This is a close-up image — 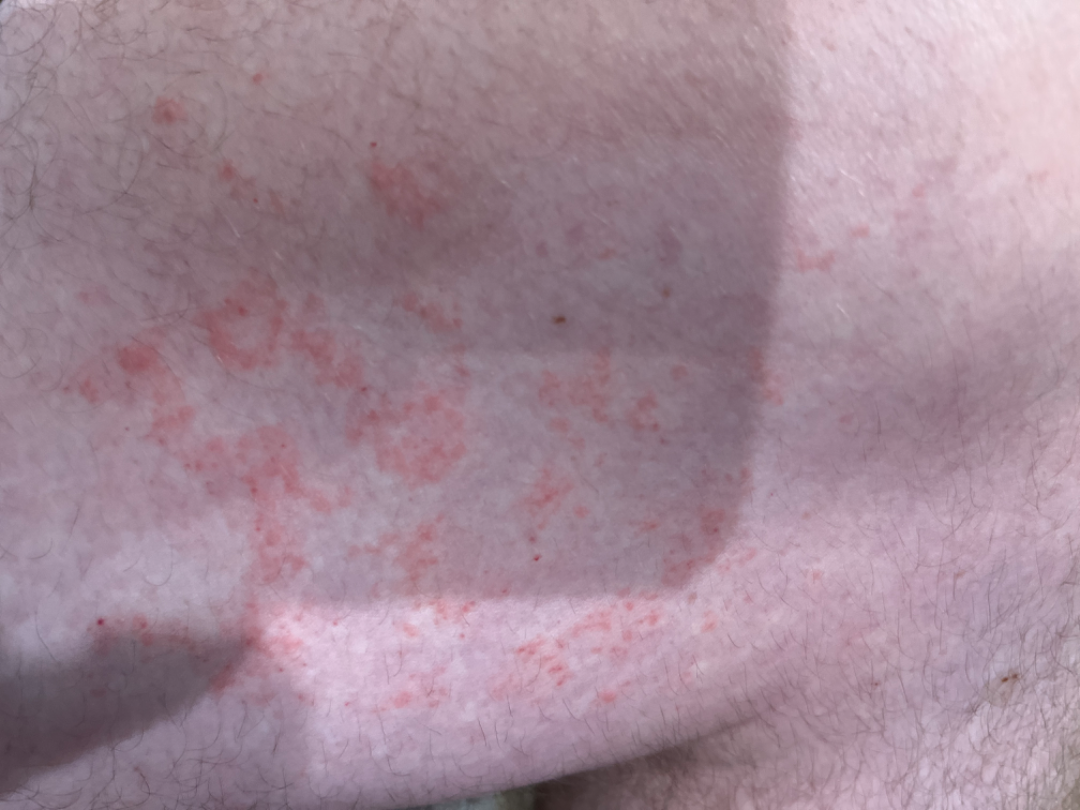The reviewer was unable to grade this case for skin condition.